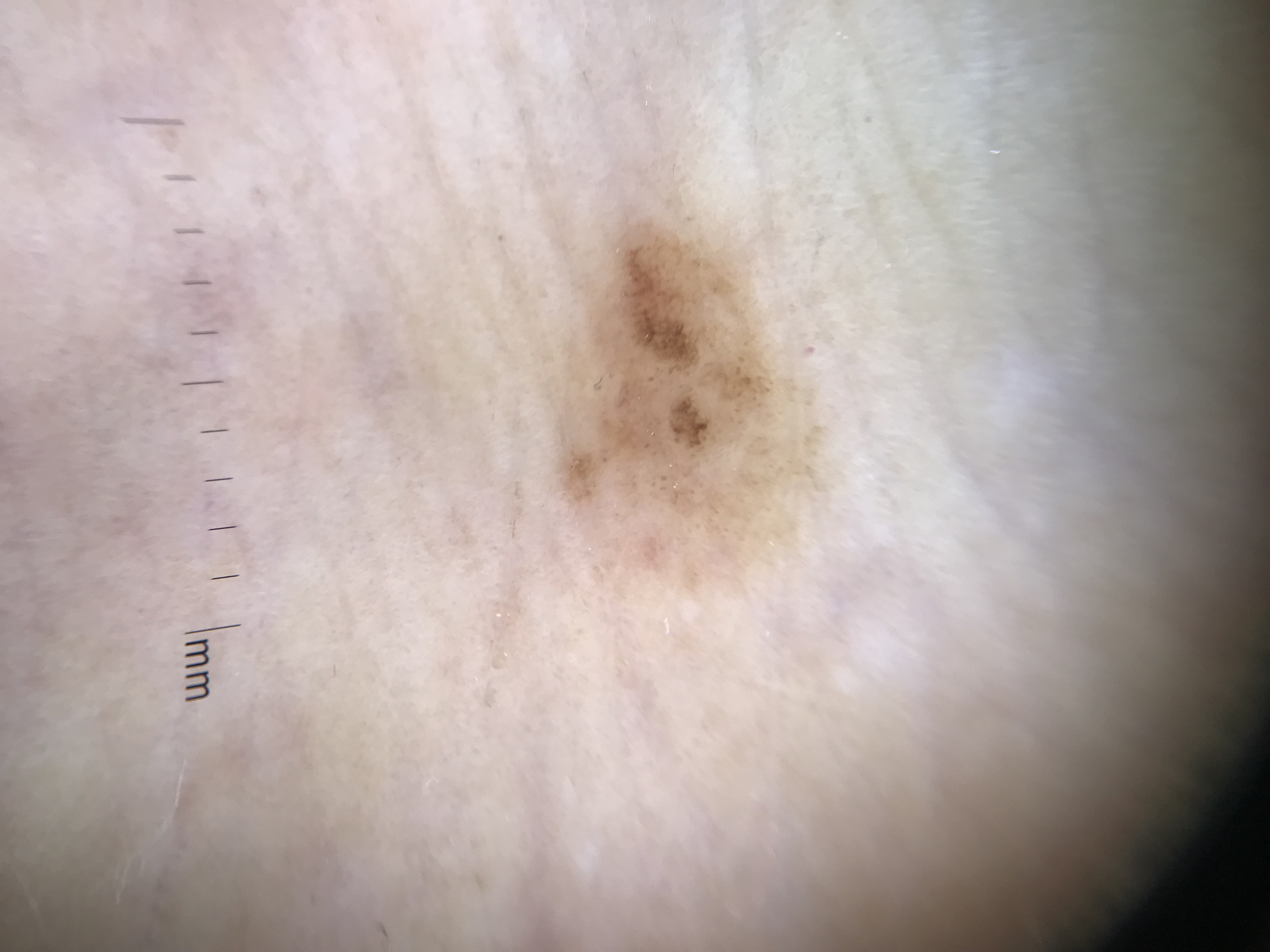{
  "image": "dermatoscopy",
  "diagnosis": {
    "name": "acral compound nevus",
    "code": "acb",
    "malignancy": "benign",
    "super_class": "melanocytic",
    "confirmation": "expert consensus"
  }
}